The subject is a male approximately 50 years of age, a dermoscopic close-up of a skin lesion.
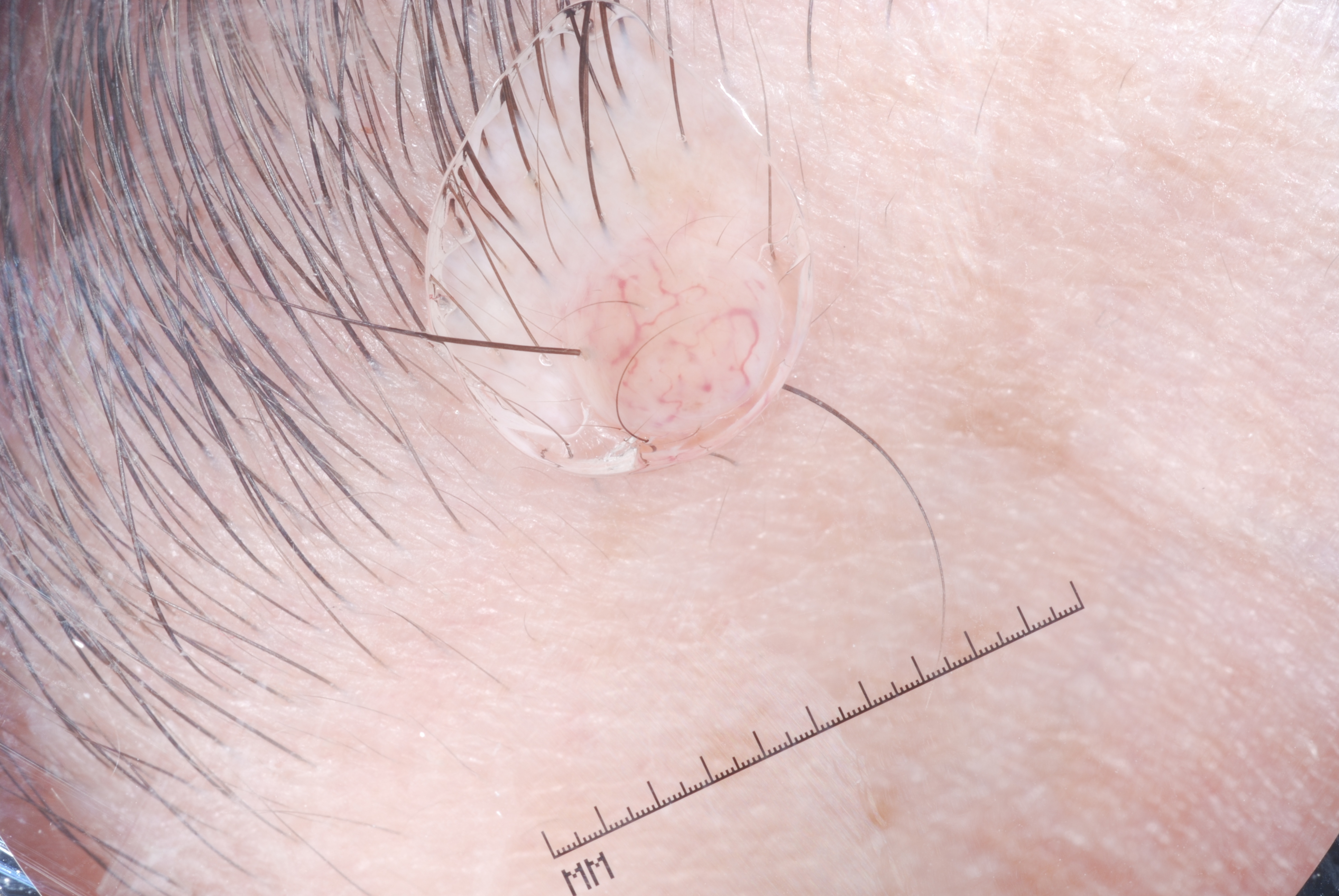location: [564,223,786,451]; absent dermoscopic features: milia-like cysts, negative network, pigment network, and streaks; impression: a melanocytic nevus.